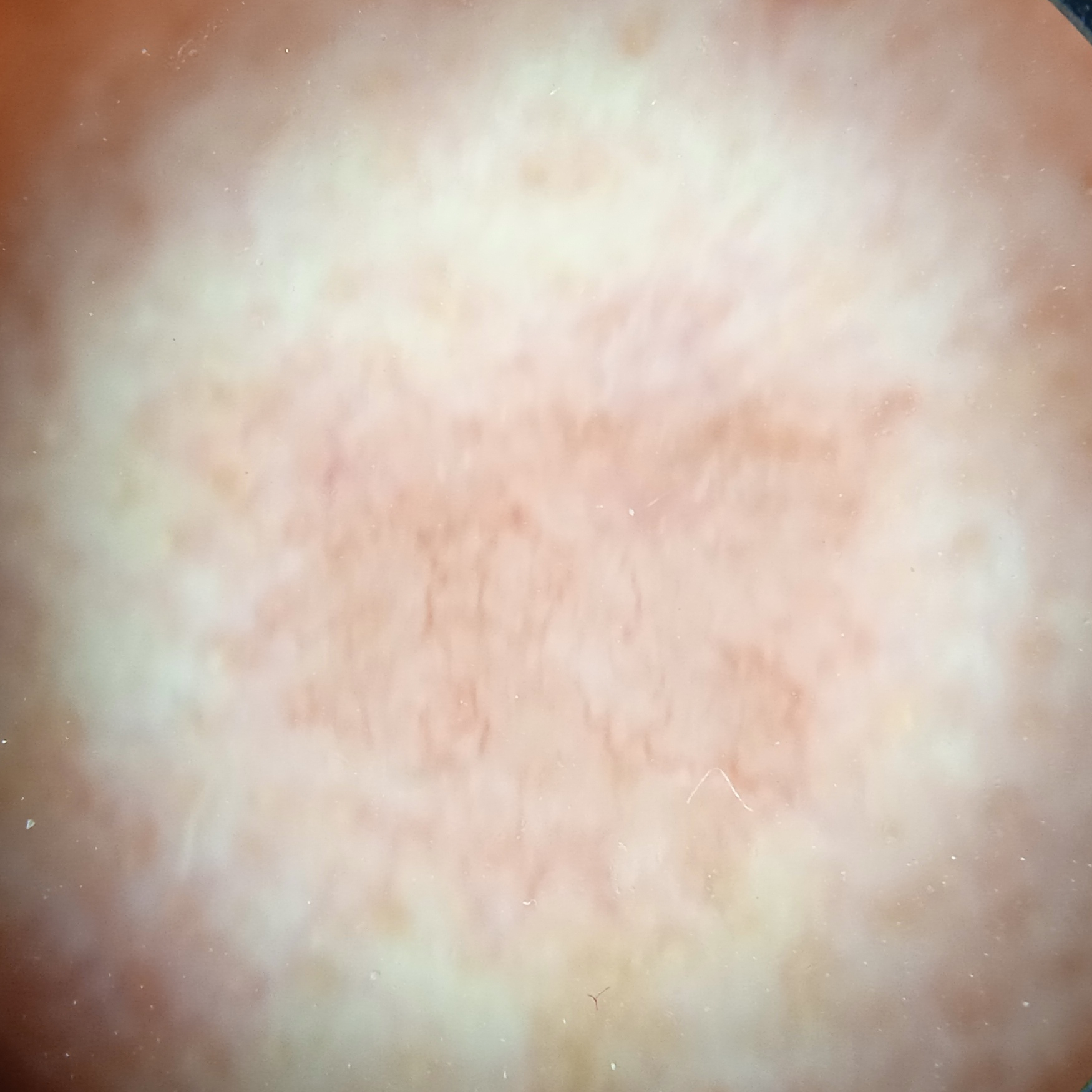| feature | finding |
|---|---|
| diagnosis | basal cell carcinoma (biopsy-proven) |